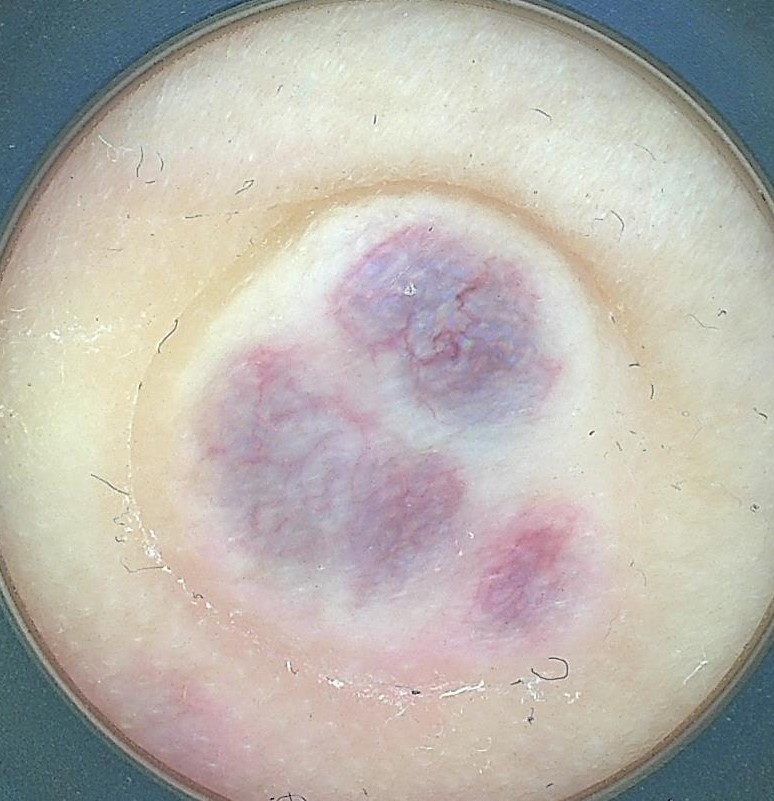| feature | finding |
|---|---|
| diagnostic label | Kaposi sarcoma (biopsy-proven) |